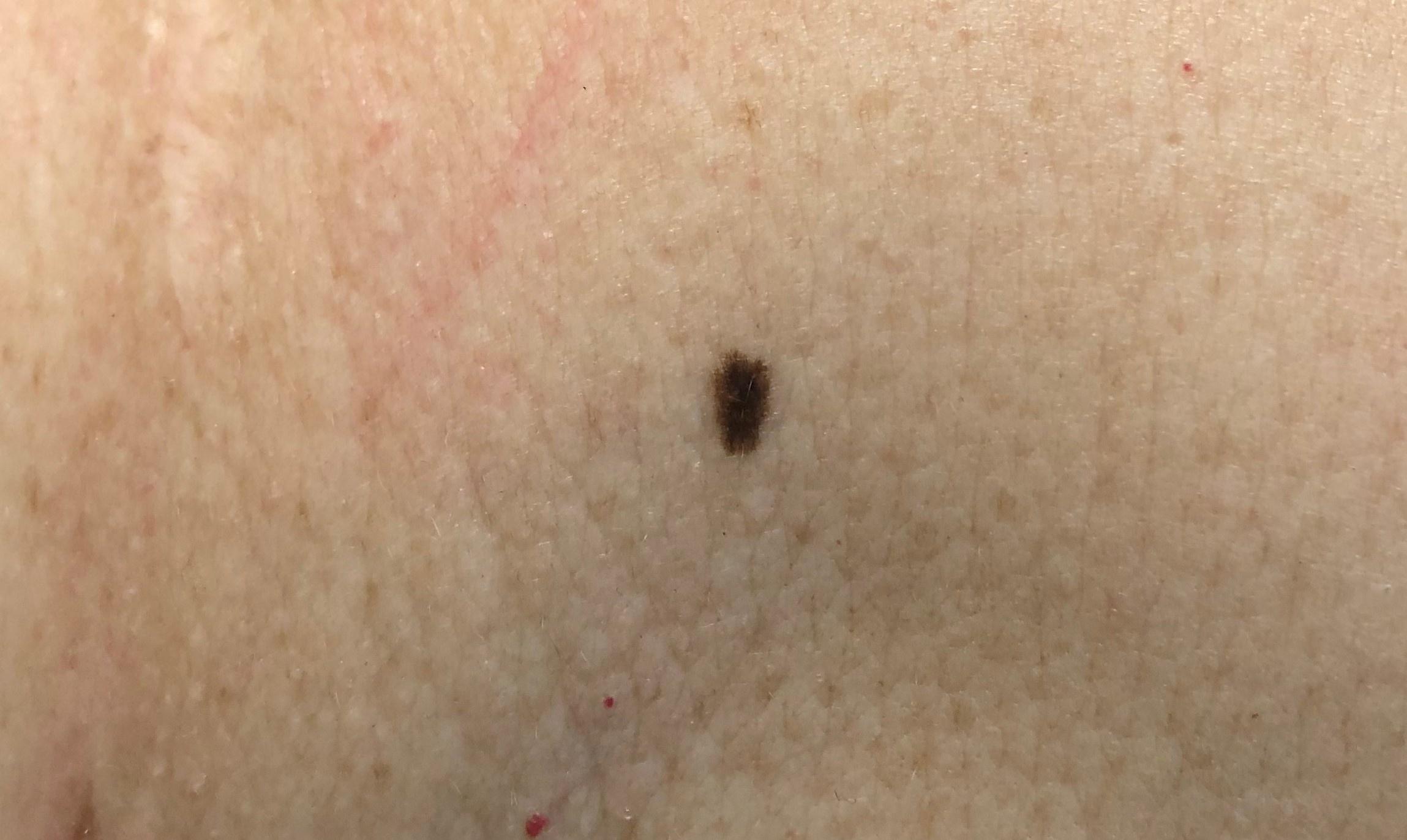A clinical photograph showing a skin lesion in context. A female patient aged 53-57. The lesion is on the trunk. Histopathological examination showed a nevus.